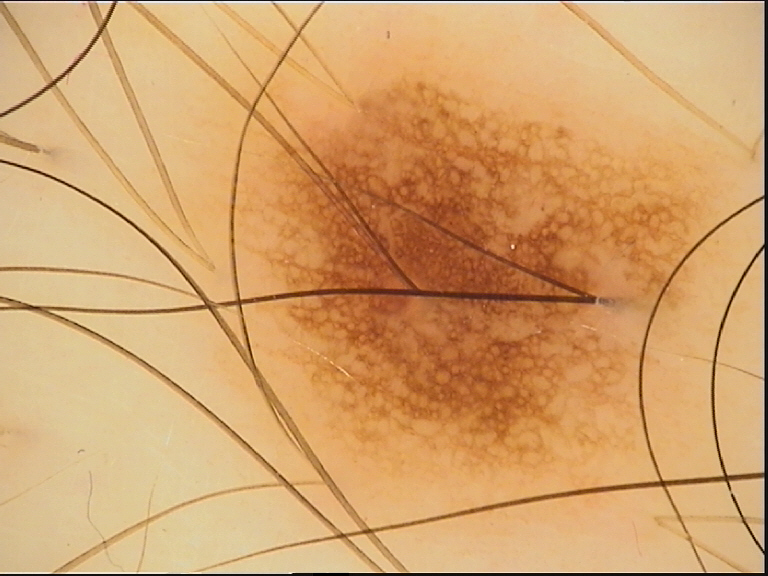Findings:
- modality: dermoscopy
- label: dysplastic junctional nevus (expert consensus)